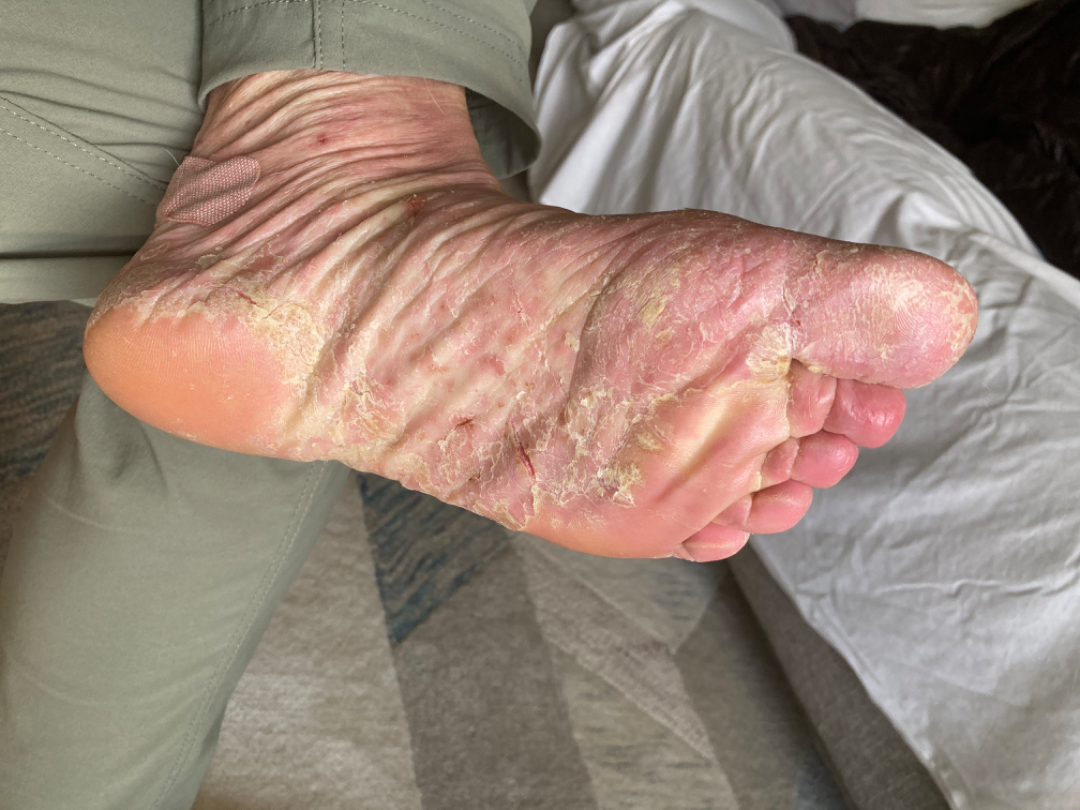Findings:
– framing: at a distance
– patient: female, age 60–69
– body site: palm, top or side of the foot and sole of the foot
– impression: the differential is split between Psoriasis and Eczema; a more distant consideration is Tinea